A dermoscopic photograph of a skin lesion: 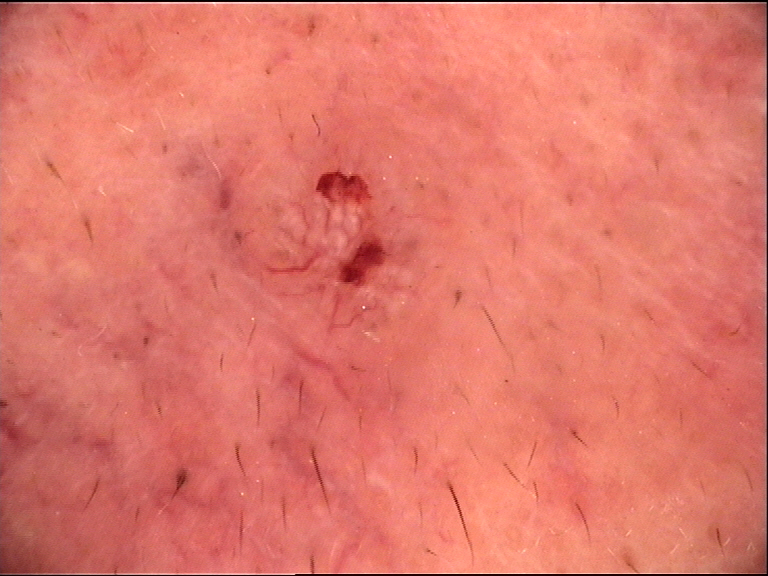Diagnosis: Histopathologically confirmed as a keratinocytic lesion — a basal cell carcinoma.